A clinical photograph of a skin lesion · the patient says their skin reddens with sun exposure · the patient describes having a moderate number of moles · a female patient 59 years old · acquired for a research image collection, with no referral diagnosis:
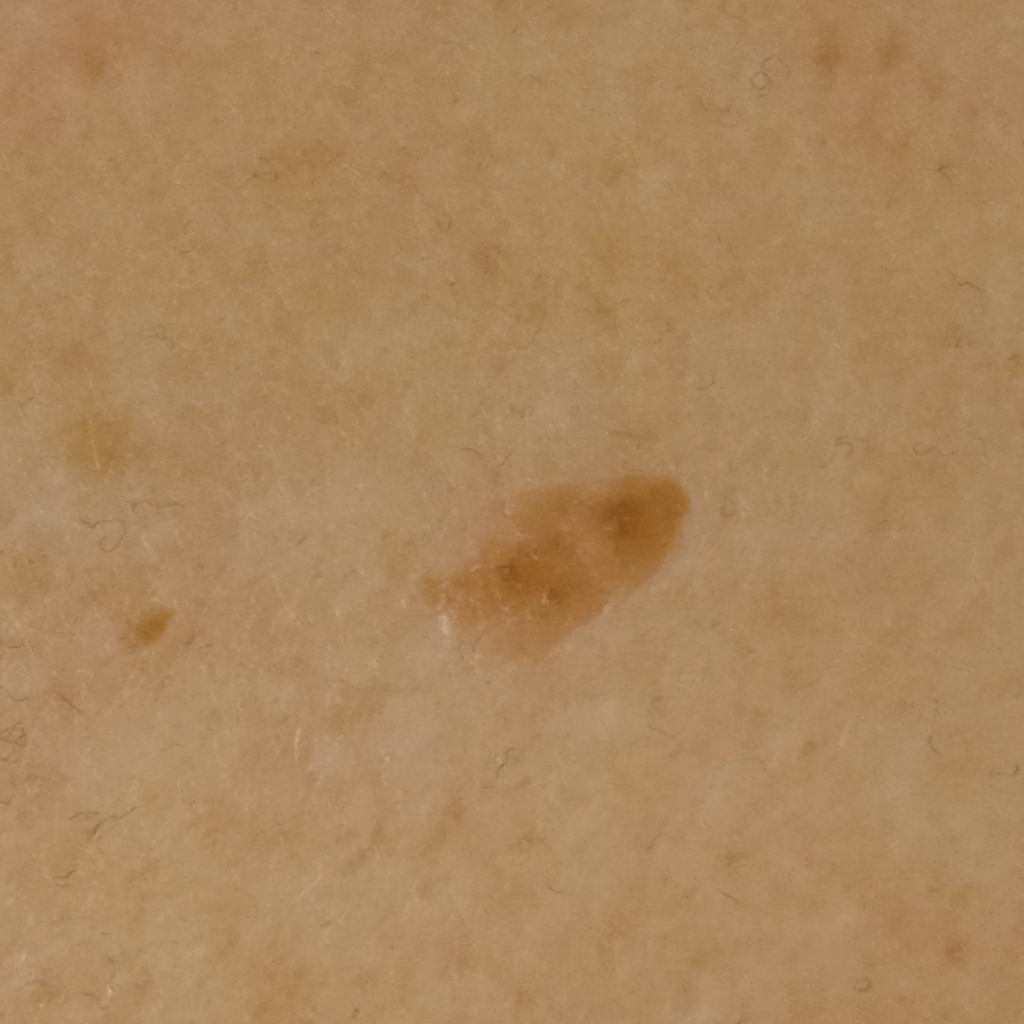| field | value |
|---|---|
| anatomic site | the torso |
| lesion size | 9.1 mm |
| diagnosis | seborrheic keratosis (dermatologist consensus) |